A dermoscopic close-up of a skin lesion.
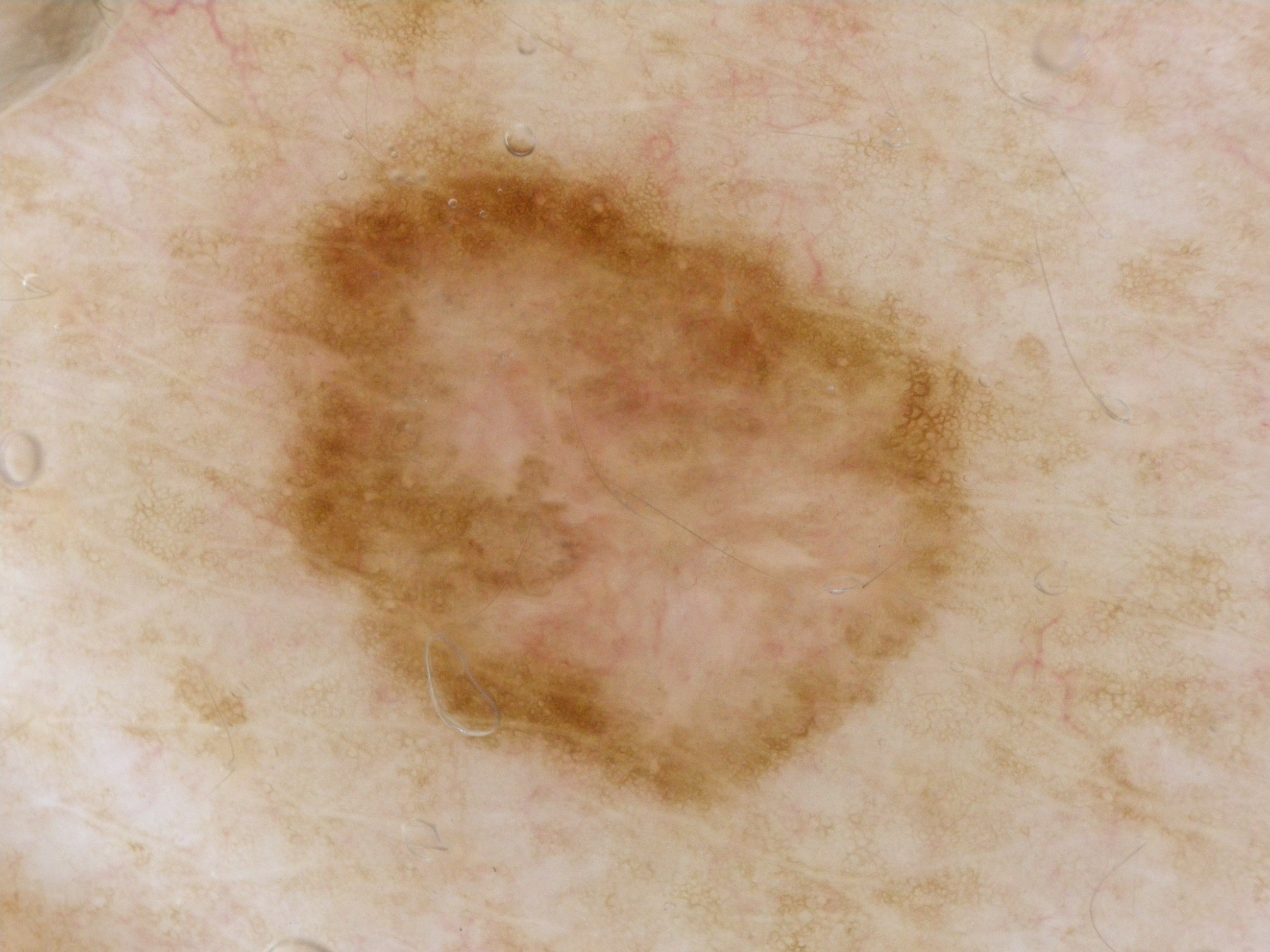Q: Which dermoscopic features were noted?
A: pigment network
Q: Where is the lesion located?
A: (257, 126, 973, 810)
Q: What is this lesion?
A: a melanoma